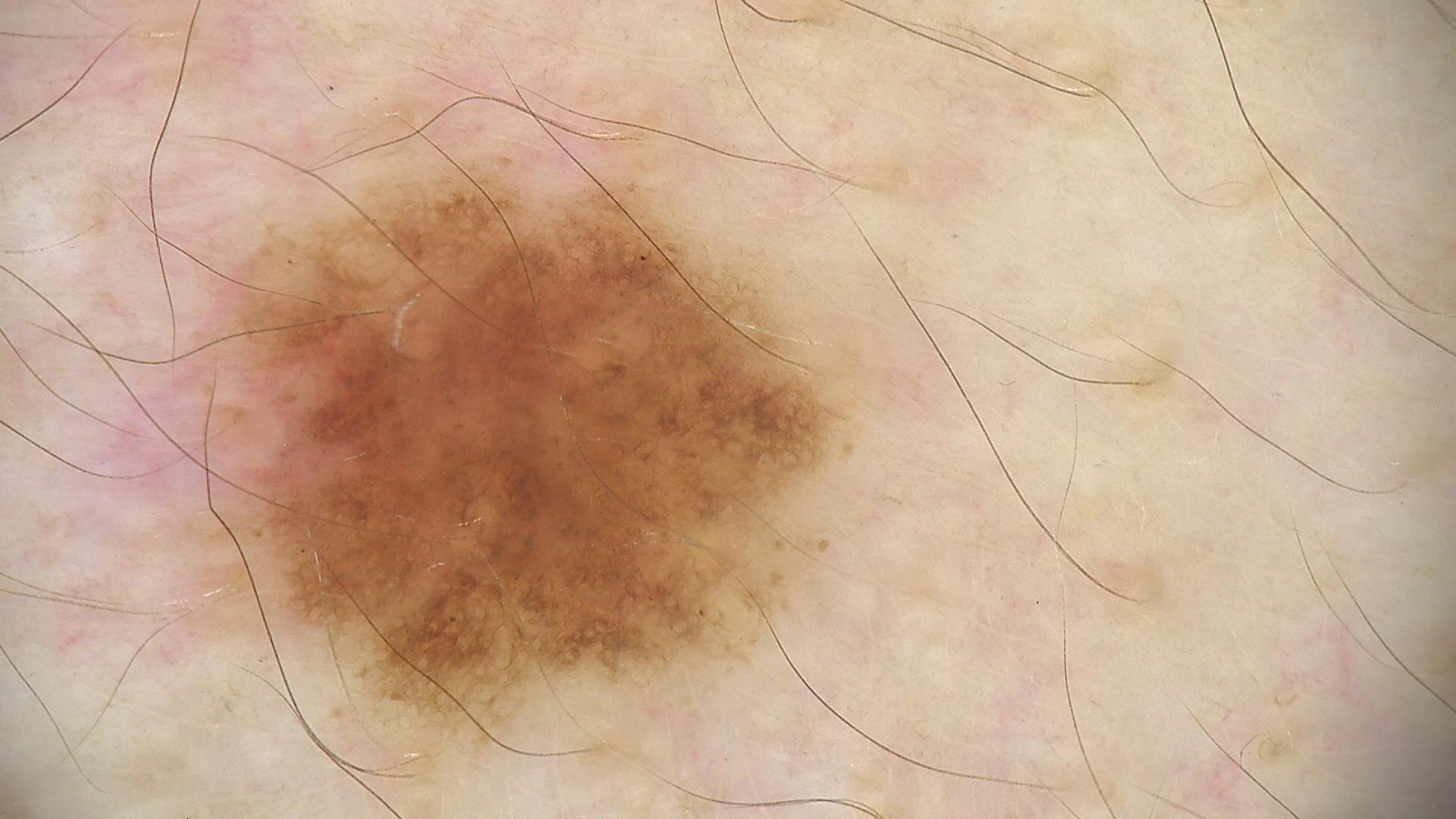assessment: dysplastic junctional nevus (expert consensus)